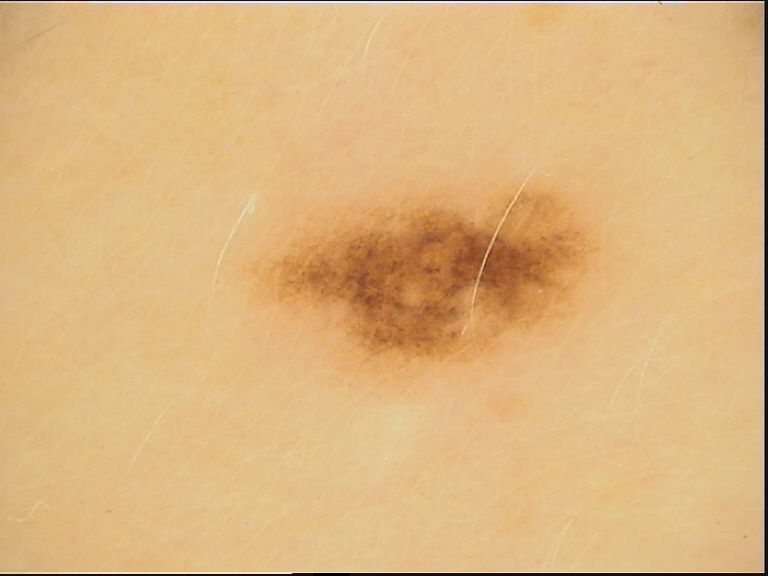A dermatoscopic image of a skin lesion. Consistent with a dysplastic compound nevus.